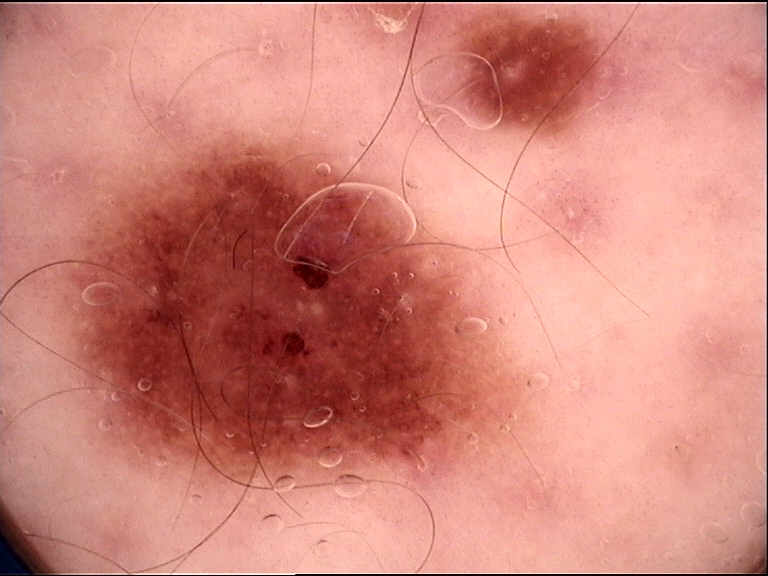Labeled as a dysplastic junctional nevus.